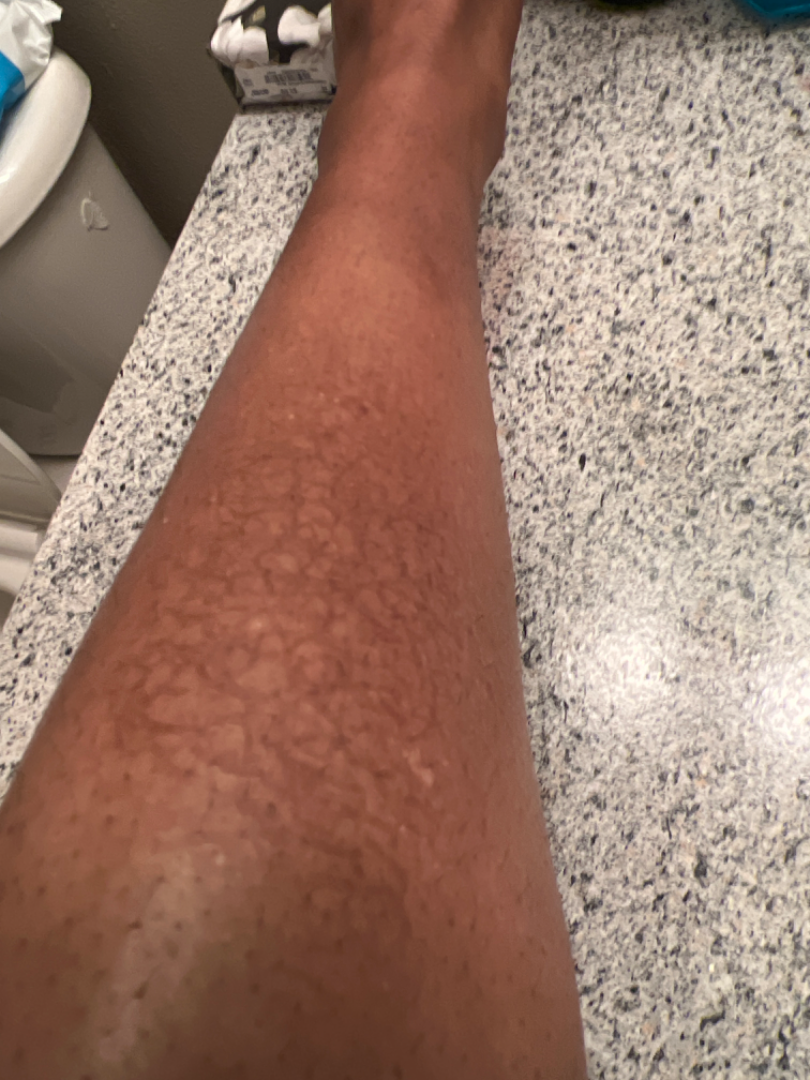Findings:
– photo taken · close-up
– clinical impression · favoring Eczema; also raised was Stasis Dermatitis; also on the differential is Ichthyosis